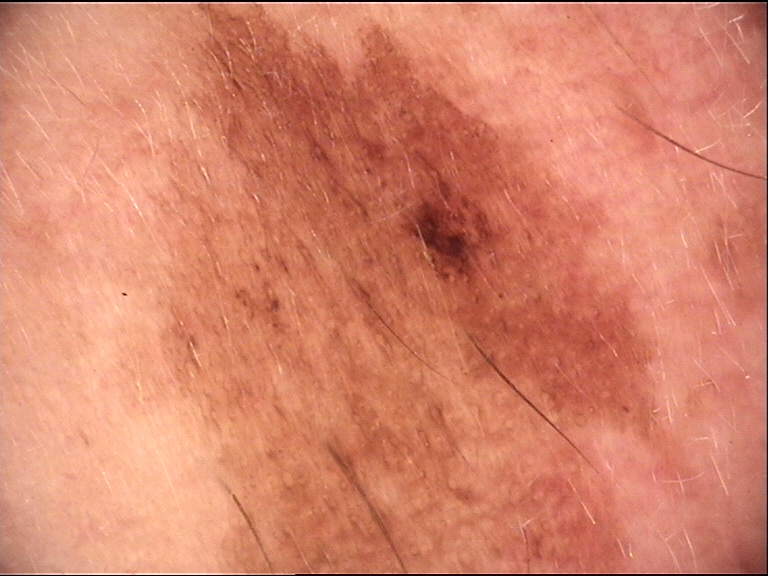Biopsy-confirmed as a lentigo maligna.